The affected area is the sole of the foot. The subject is a female aged 30–39. The photo was captured at a distance:
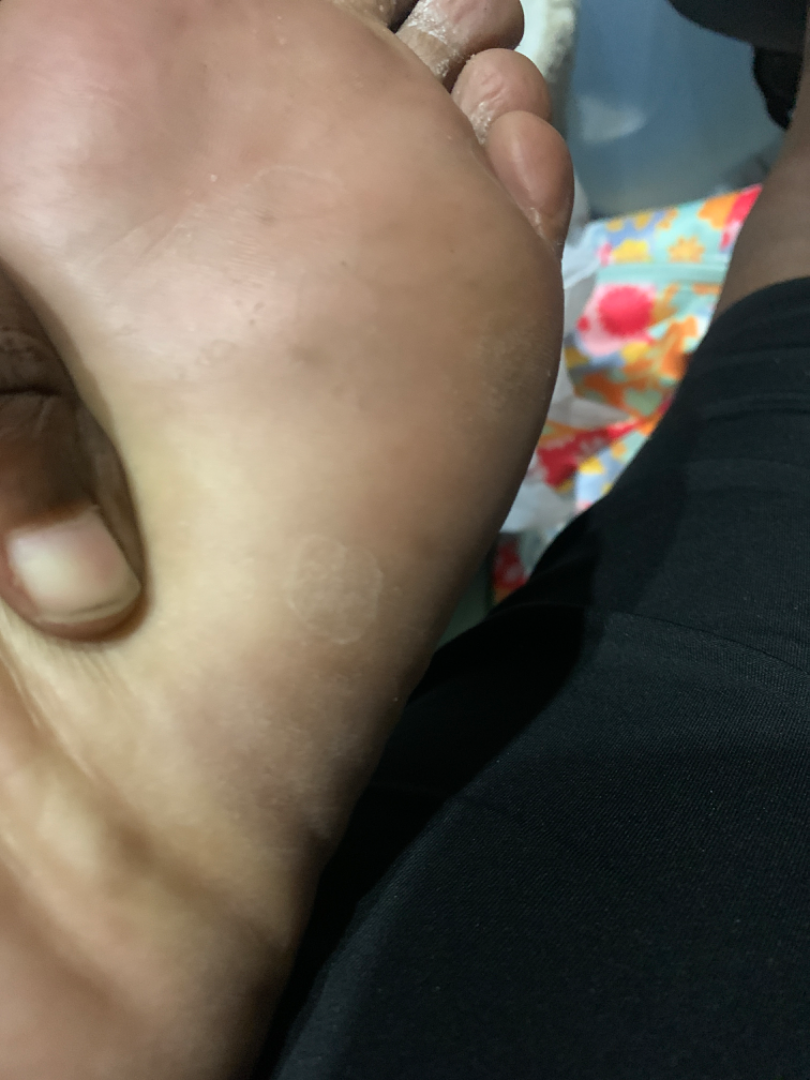assessment: not assessable